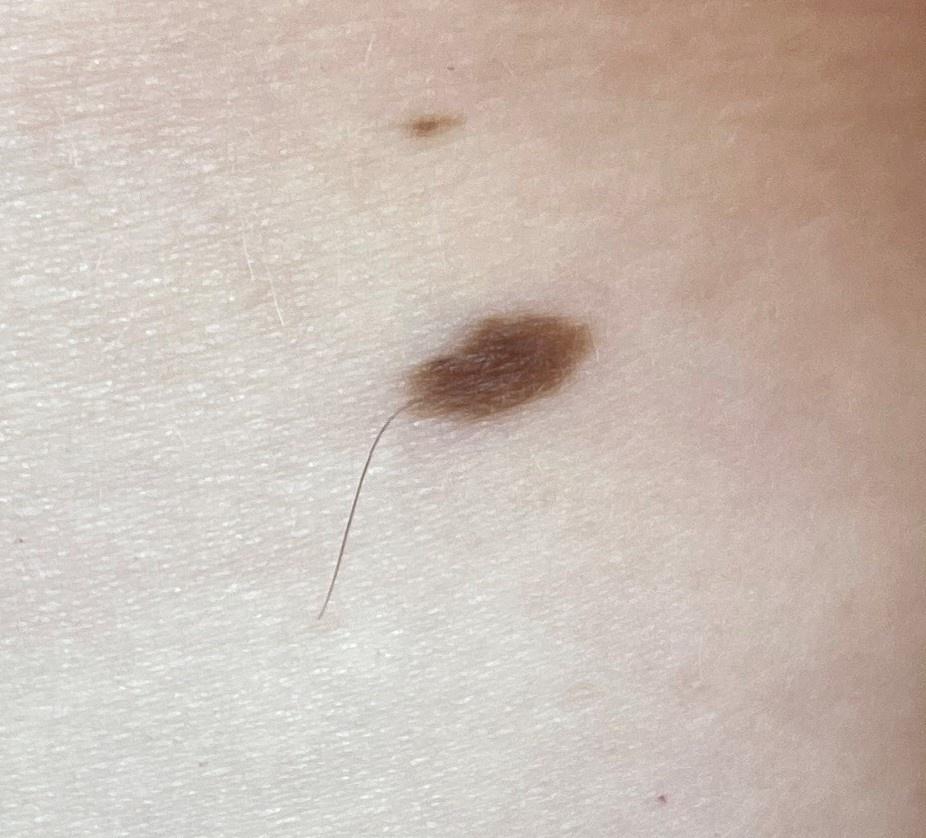Impression: The clinical assessment was a nevus.